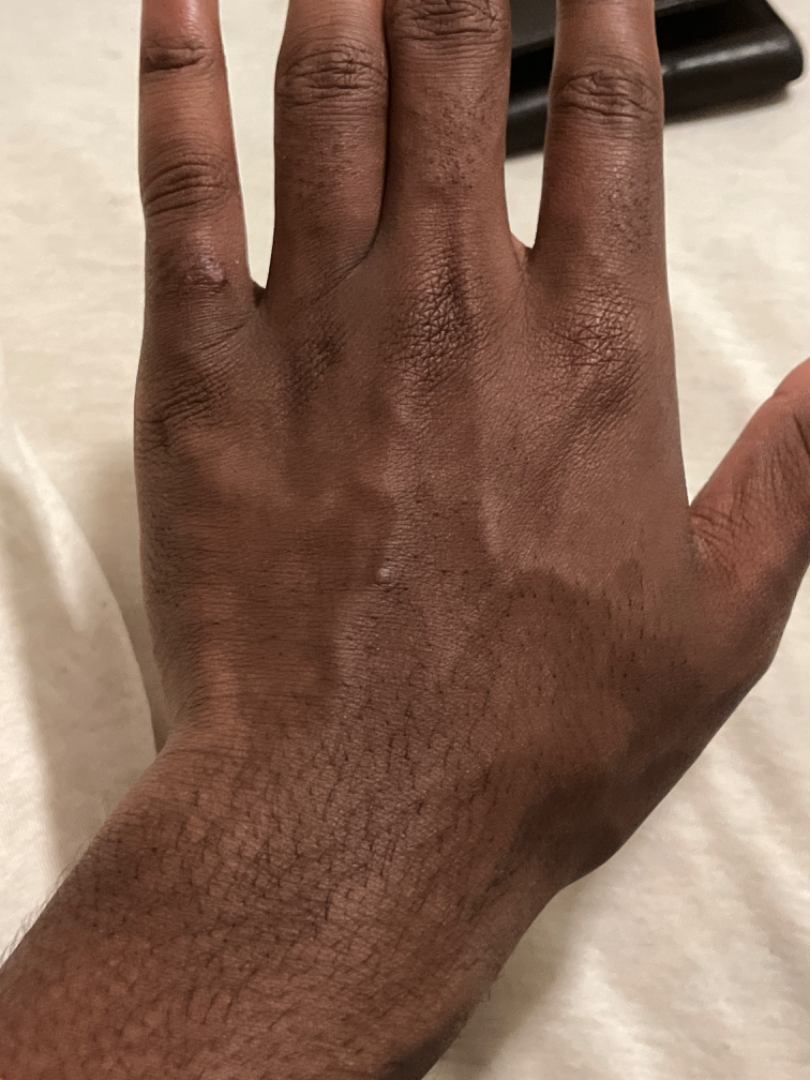This is a close-up image. On remote review of the image: most consistent with Prurigo nodularis; also consider Calcinosis cutis.